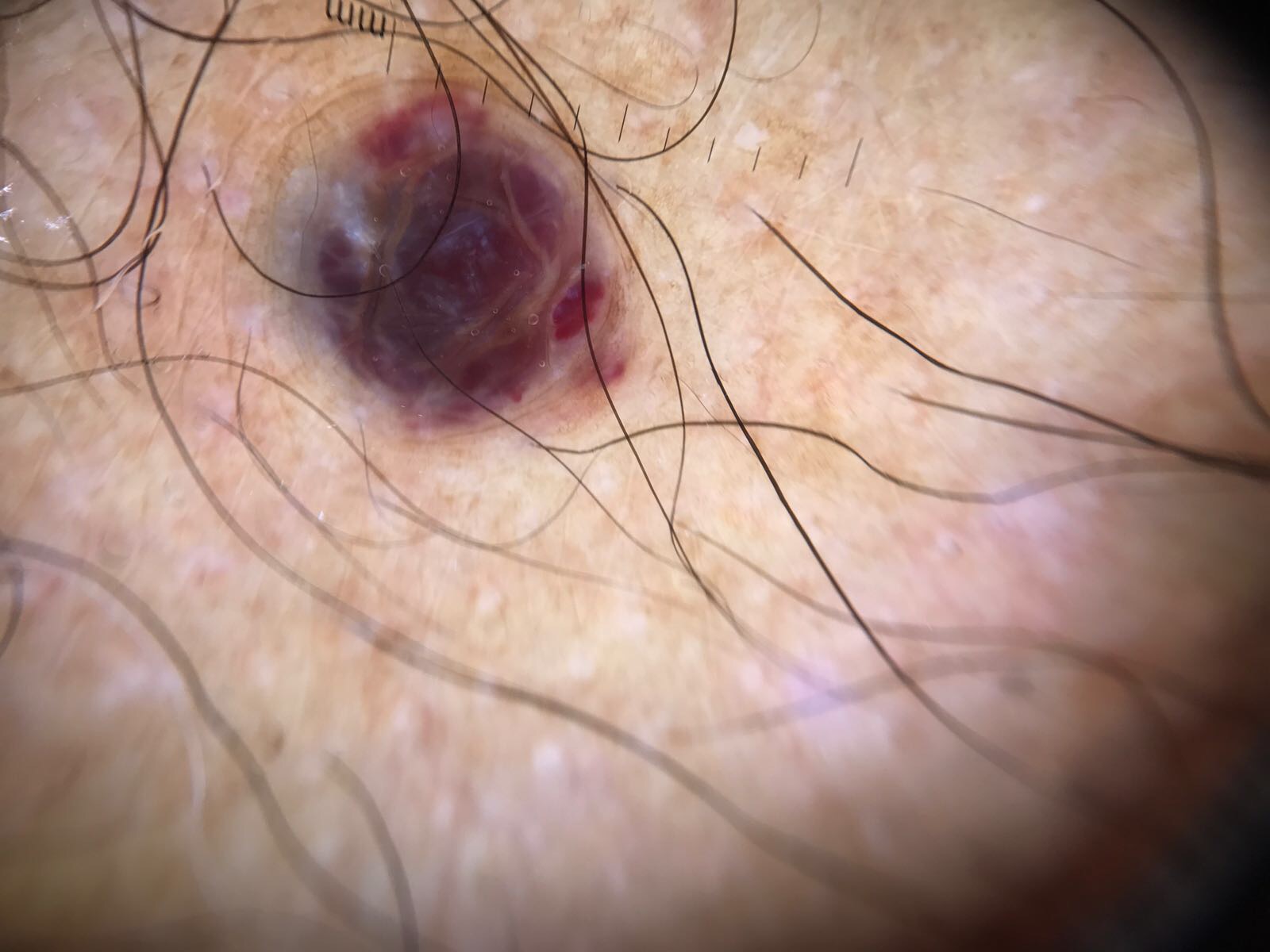Case:
A dermoscopic image of a skin lesion. The architecture is that of a vascular lesion.
Conclusion:
Diagnosed as a hemangioma.